A female patient approximately 30 years of age. A skin lesion imaged with contact-polarized dermoscopy. The patient is FST II.
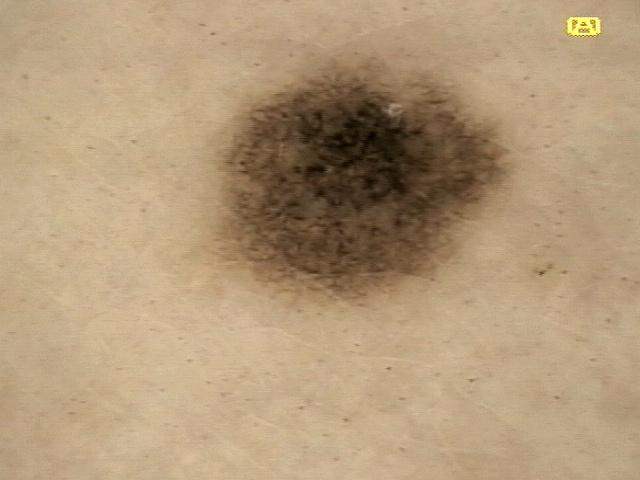Q: Where is the lesion located?
A: the trunk
Q: What is this lesion?
A: Nevus